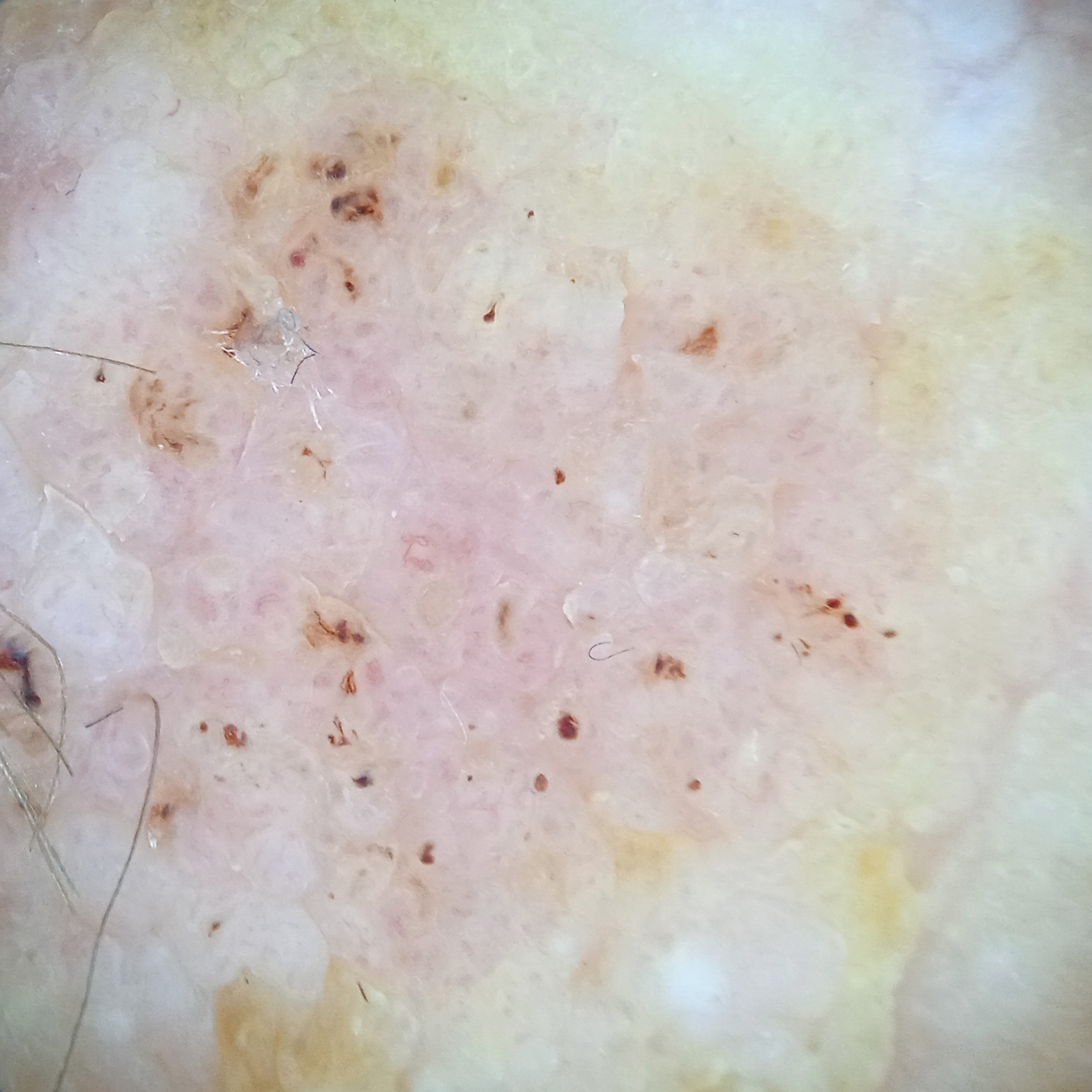A female subject aged 81. A moderate number of moles by the patient's own estimate. Collected as part of a research study, without a referral diagnosis. The patient says their skin reddens painfully with sun exposure. A skin lesion imaged with a dermatoscope. The lesion is on the face. The lesion measures approximately 36.6 mm. The consensus diagnosis for this lesion was a seborrheic keratosis.